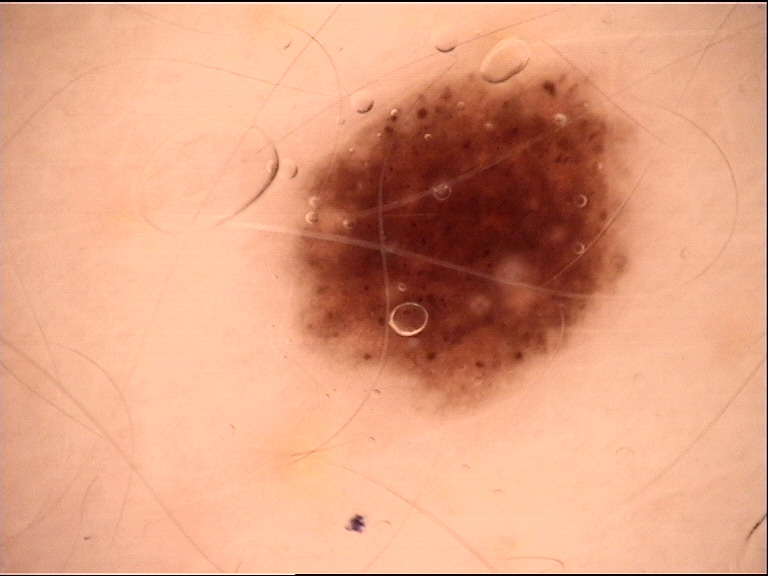Summary:
A dermatoscopic image of a skin lesion.
Impression:
The diagnosis was a banal lesion — a junctional nevus.